A close-up photograph: 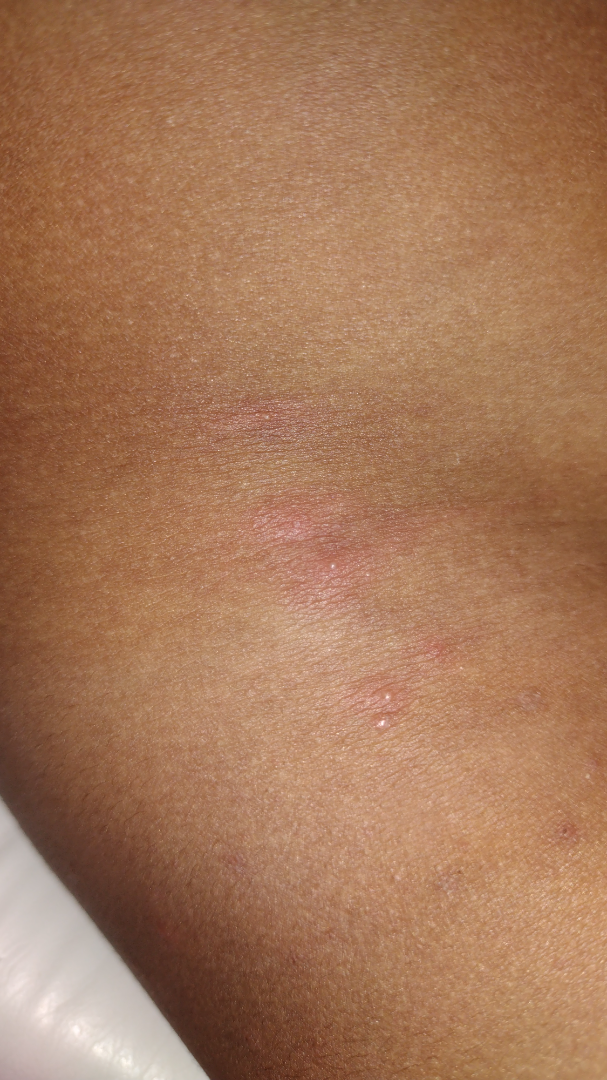Impression: The reviewing dermatologist was unable to assign a differential diagnosis from the image.